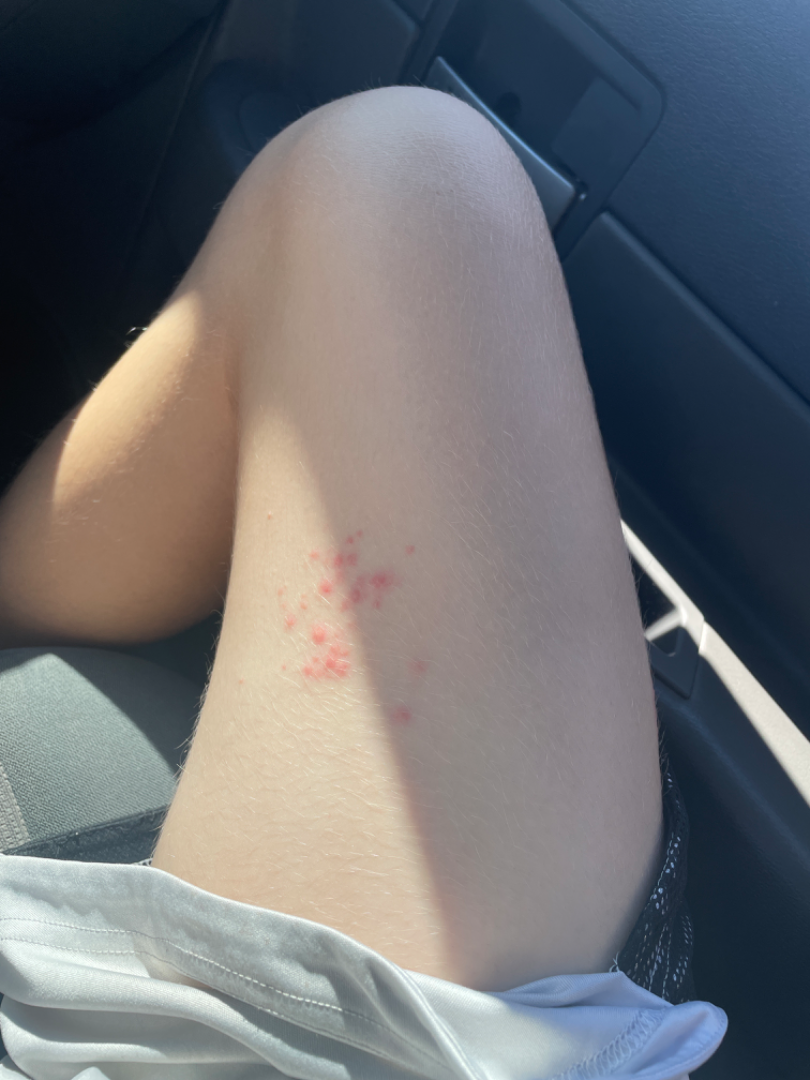dermatologist impression: the differential, in no particular order, includes Folliculitis, Herpes Zoster and Herpes Simplex.